Female patient, age 40–49; the leg is involved; this image was taken at a distance — 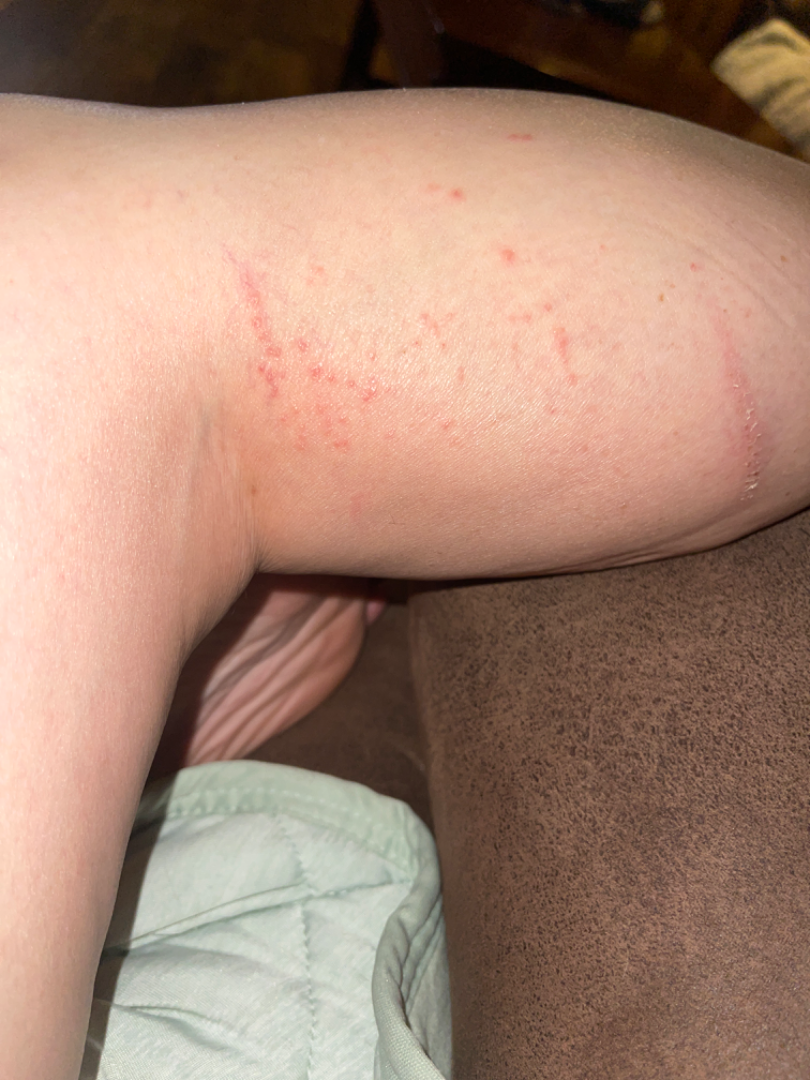Review: The condition could not be reliably identified from the image.